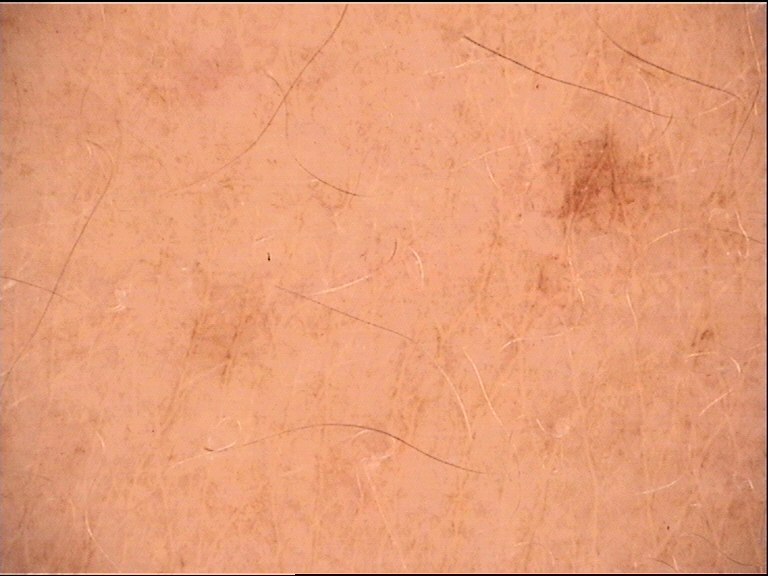The diagnostic label was a benign lesion — a solar lentigo.